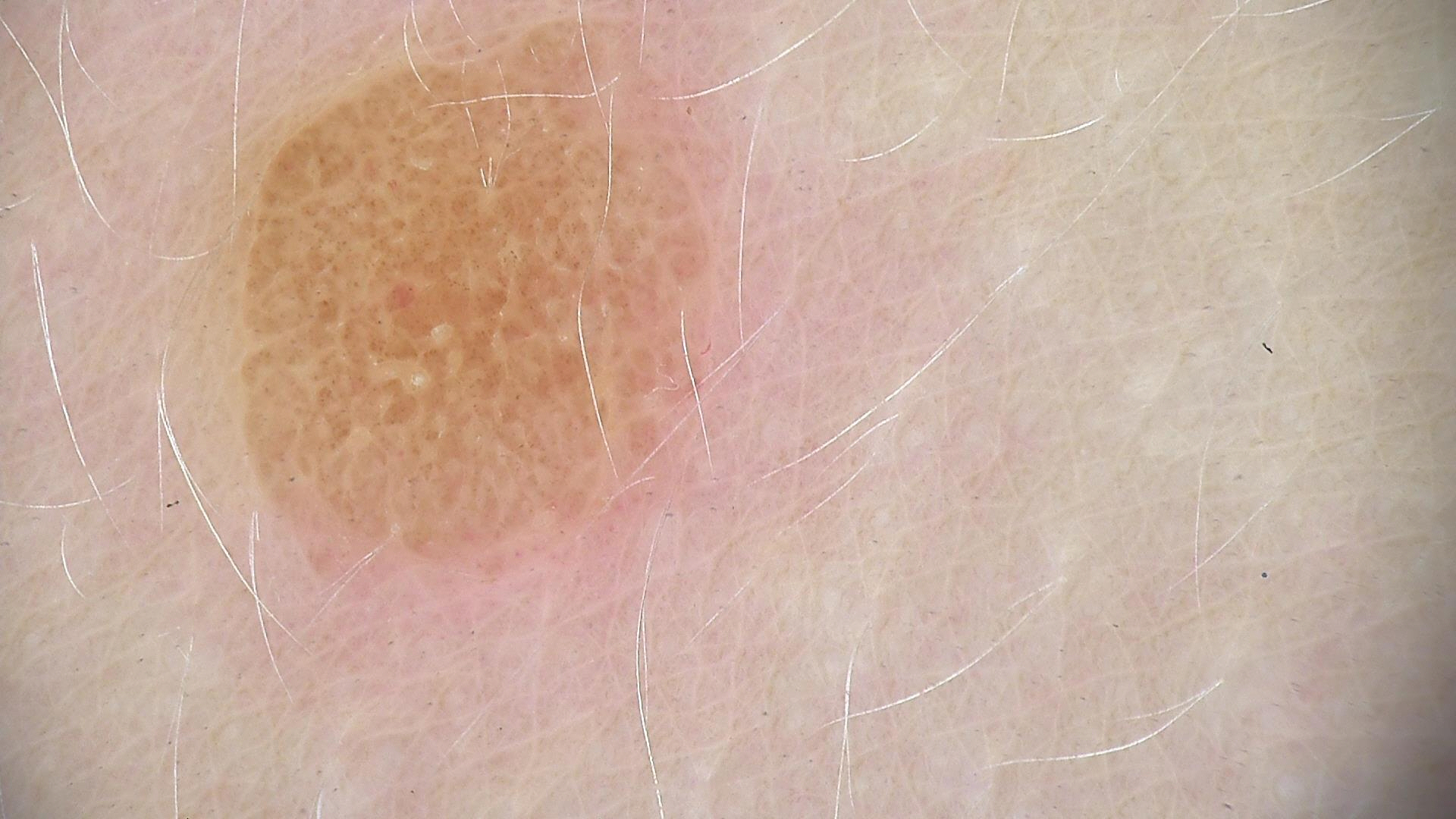A dermatoscopic image of a skin lesion.
The morphology is that of a banal lesion.
The diagnostic label was a compound nevus.